The patient is FST III. A contact-polarized dermoscopy image of a skin lesion. A male subject aged 38-42. The chart records no previous melanoma and no first-degree relative with melanoma — 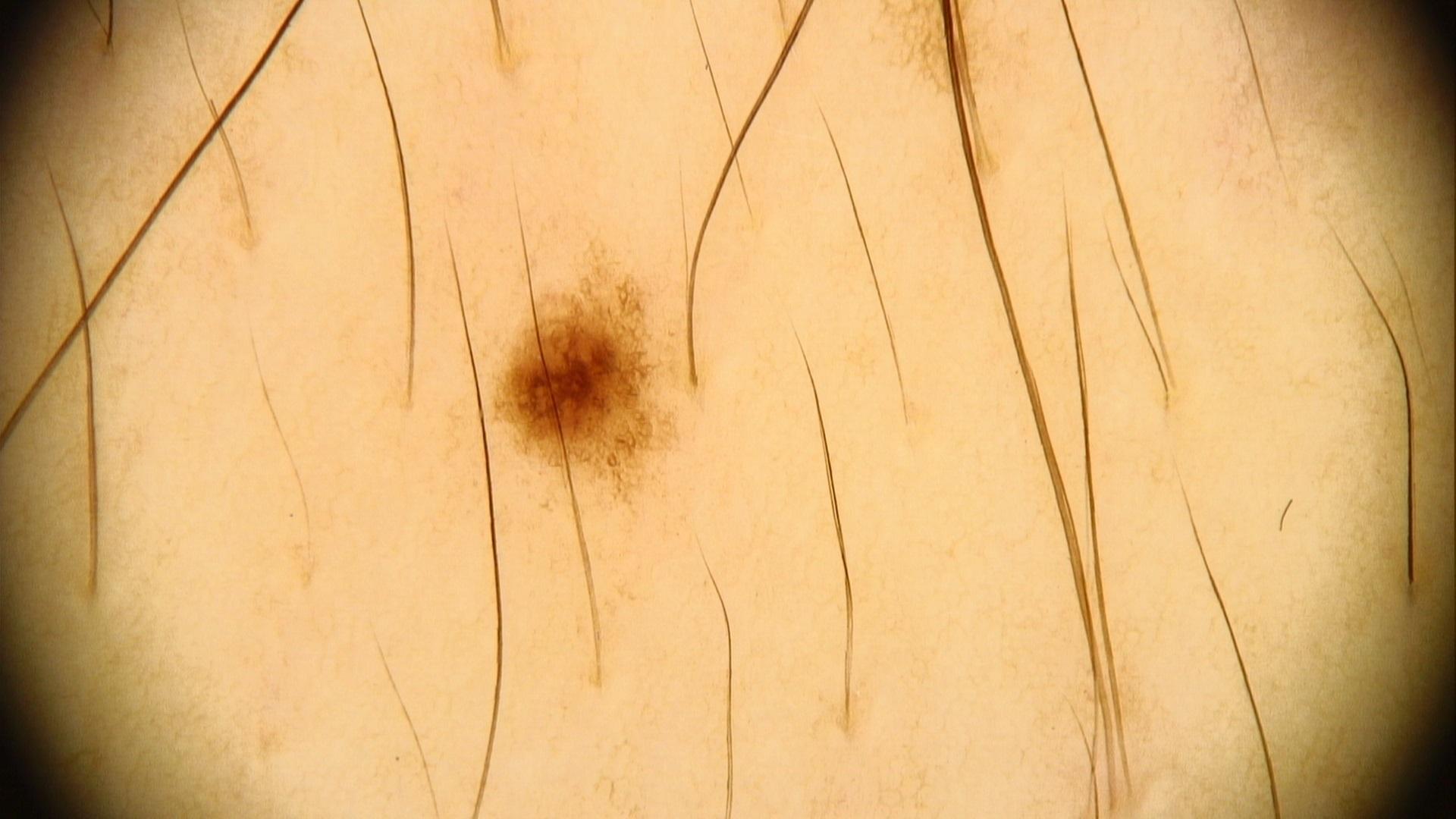Clinical context: The lesion is on the trunk. Conclusion: Clinically diagnosed as a benign, melanocytic lesion — a nevus.